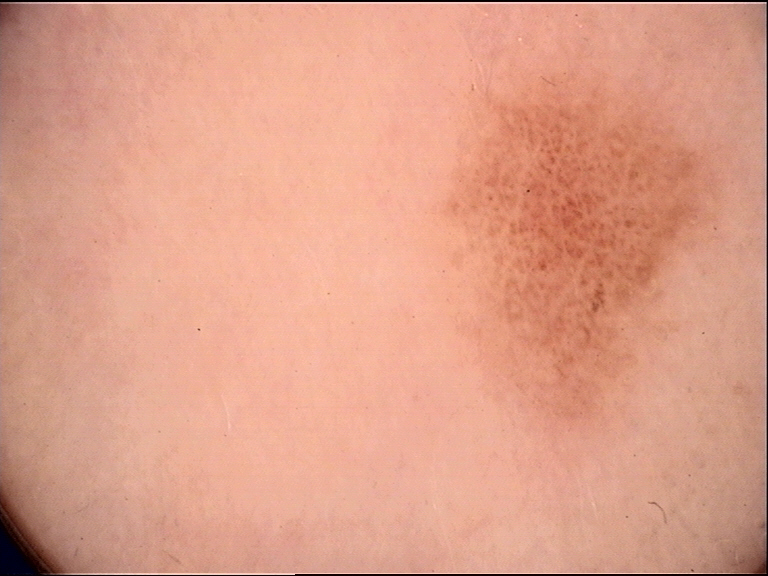{"image": "dermatoscopy", "diagnosis": {"name": "dysplastic junctional nevus", "code": "jd", "malignancy": "benign", "super_class": "melanocytic", "confirmation": "expert consensus"}}